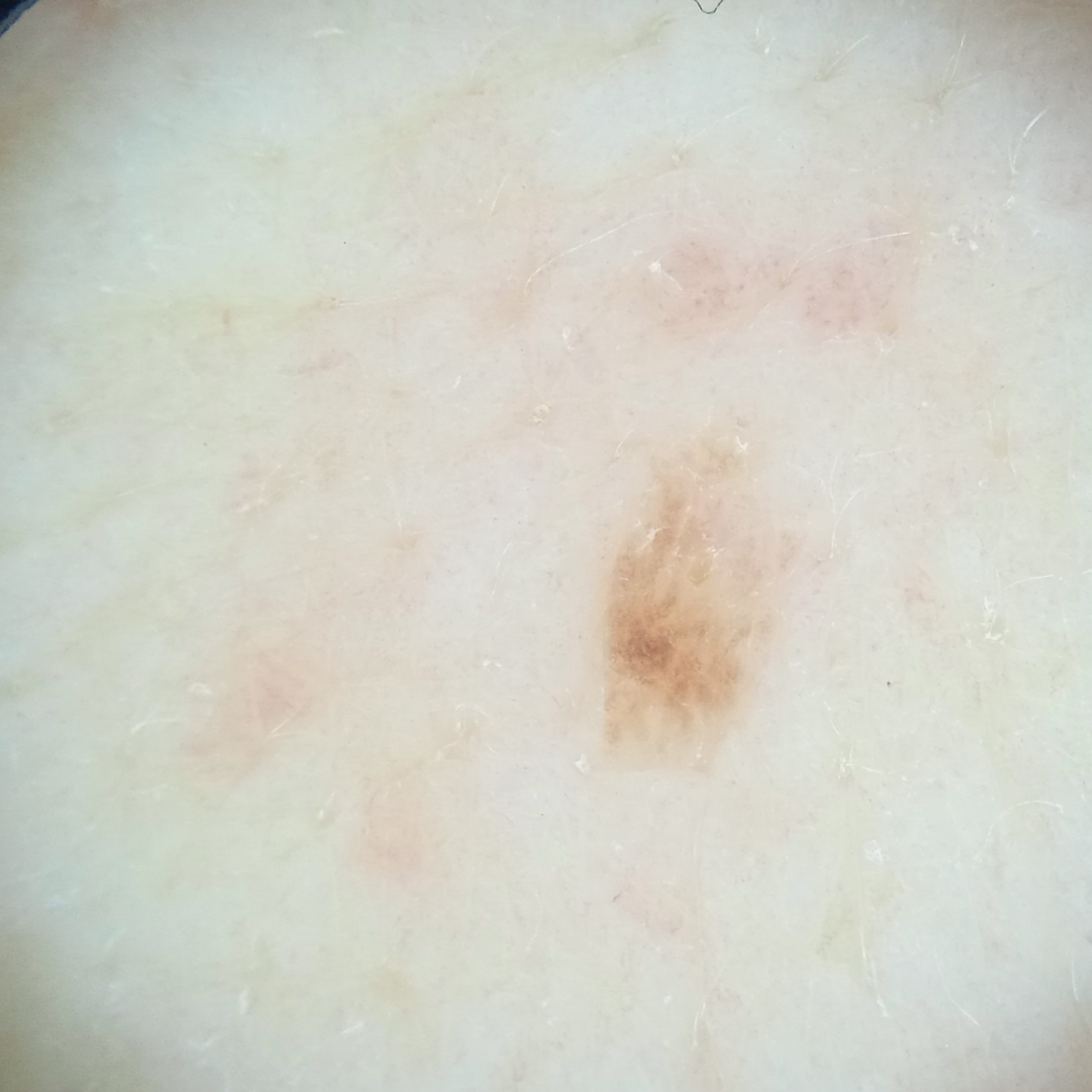A female patient 71 years old. Dermoscopy of a skin lesion. The patient reports a personal history of skin cancer and a personal history of cancer. The patient describes having few moles overall. The patient says their skin reddens with sun exposure. Collected as part of a research study, without a referral diagnosis. The lesion is on the back. Measuring roughly 3.8 mm. The lesion was assessed as a seborrheic keratosis.